A skin lesion imaged with a dermatoscope. A female subject, in their 40s:
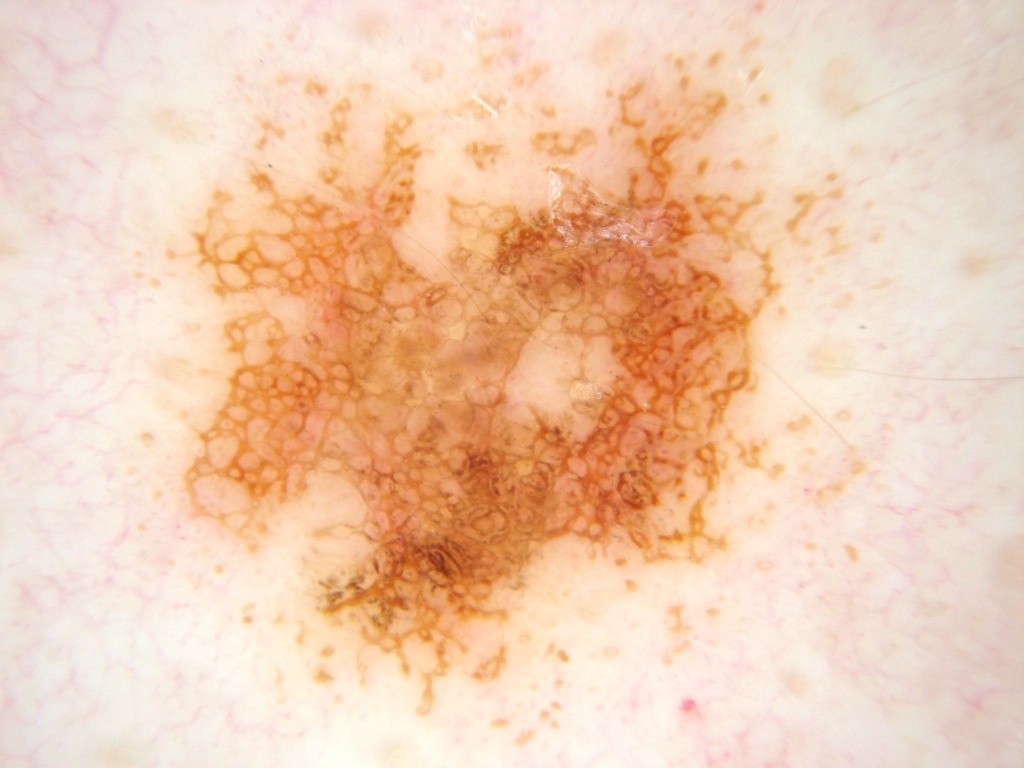Case summary:
The dermoscopic pattern shows pigment network and globules, with no milia-like cysts, negative network, or streaks. The lesion is located at x1=121 y1=19 x2=906 y2=760. The lesion occupies roughly 61% of the field.
Impression:
The lesion was assessed as a melanocytic nevus, a benign lesion.